A dermatoscopic image of a skin lesion. A female patient, aged 68 to 72 — 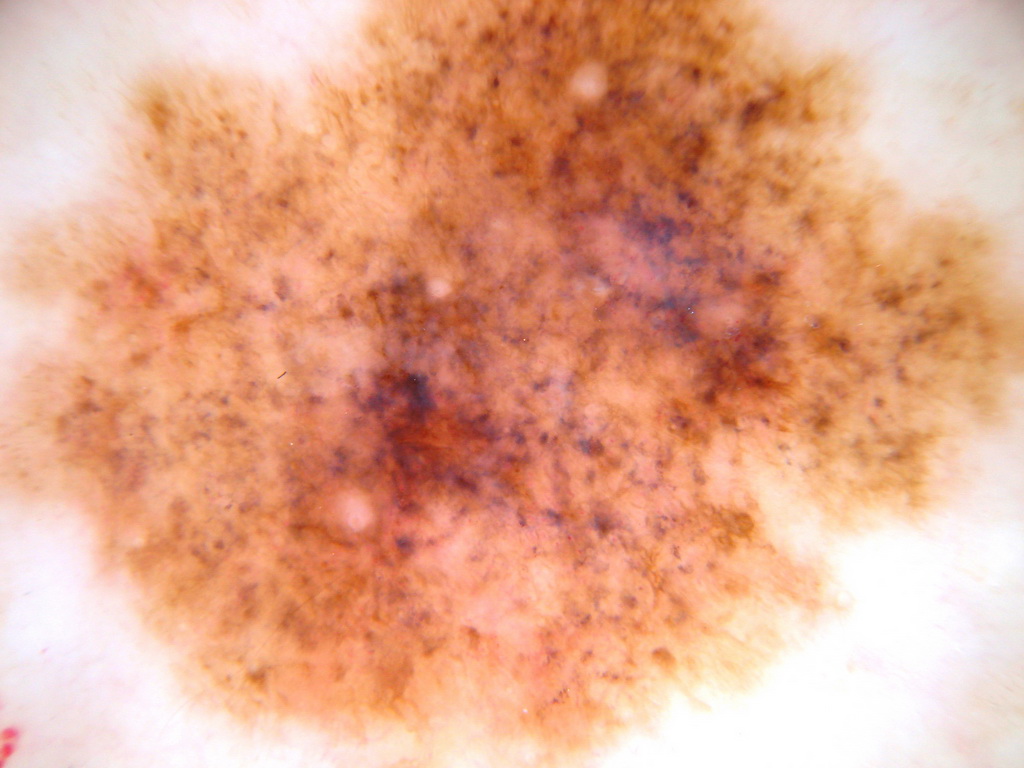The lesion extends across the full dermoscopic field.
Dermoscopic assessment notes no negative network, milia-like cysts, globules, streaks, or pigment network.
Histopathologically confirmed as a melanoma, a malignancy.